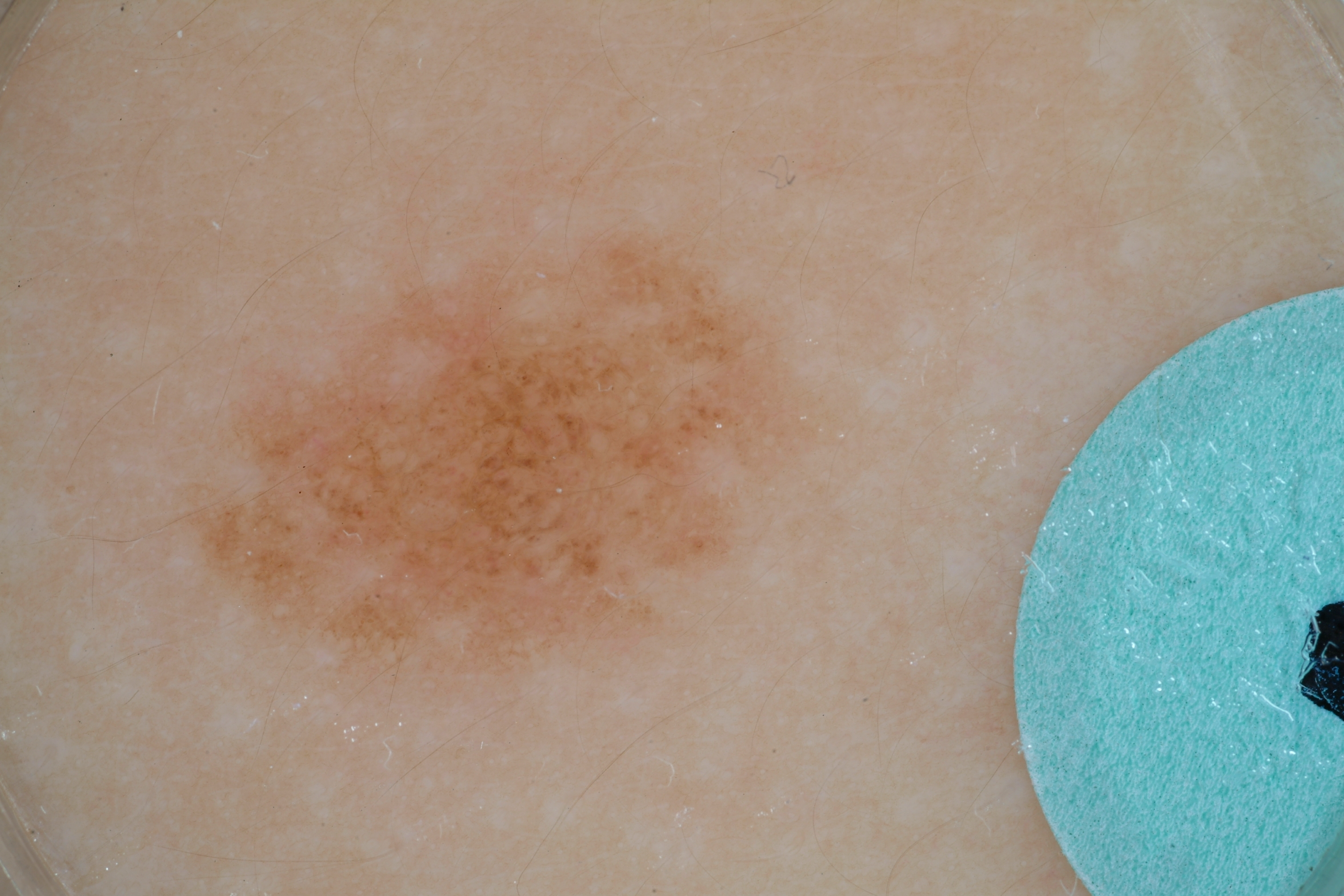A dermoscopic view of a skin lesion. Dermoscopic review identifies pigment network, with no globules, milia-like cysts, negative network, or streaks. The lesion takes up about 19% of the image. In (x1, y1, x2, y2) order, the lesion's extent is bbox=[173, 219, 851, 697]. The diagnostic assessment was a melanocytic nevus.